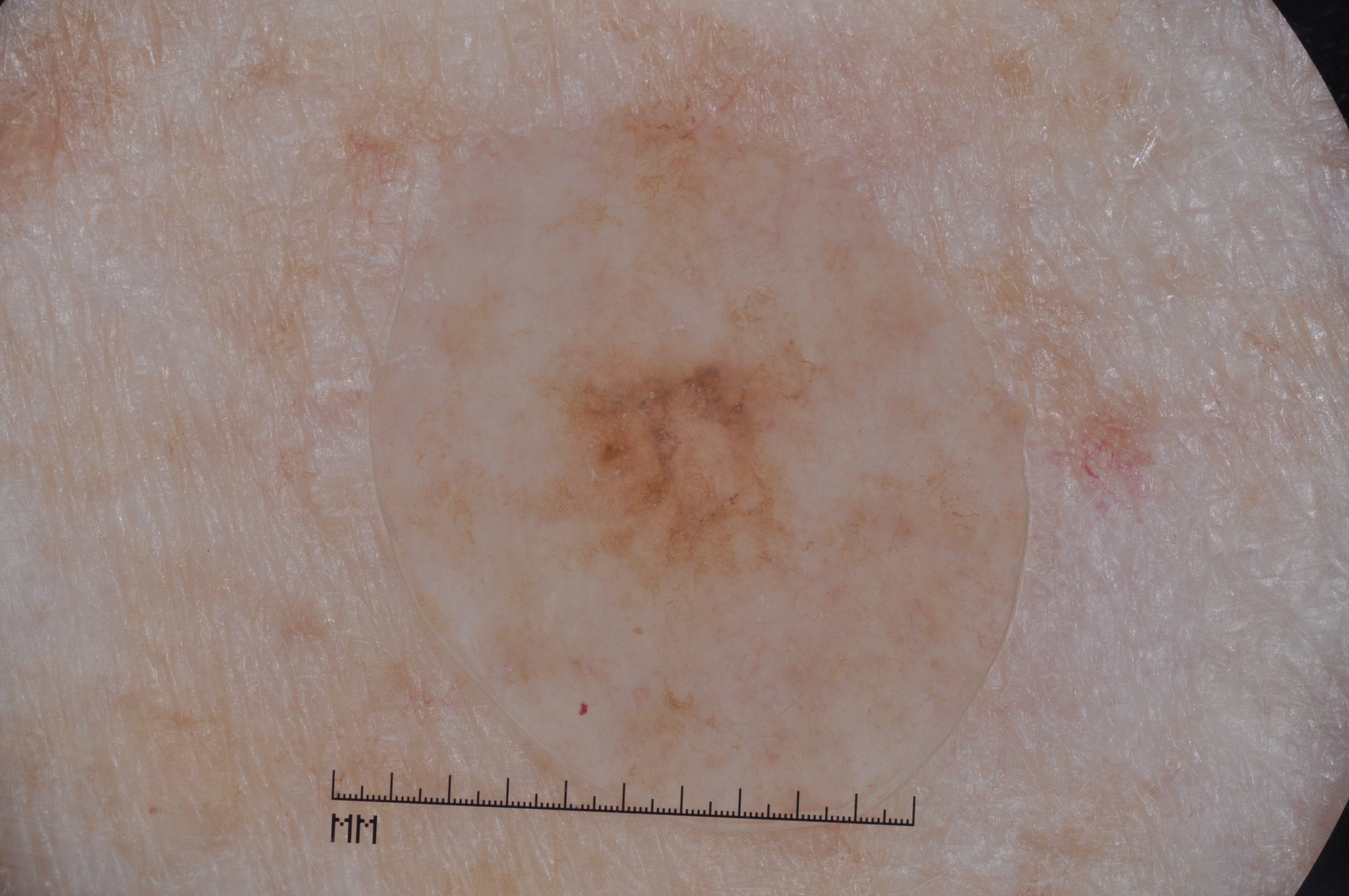{
  "image": {
    "modality": "dermoscopy"
  },
  "dermoscopic_features": {
    "present": [
      "milia-like cysts",
      "pigment network"
    ],
    "absent": [
      "streaks",
      "negative network"
    ]
  },
  "lesion_location": {
    "bbox_xyxy": [
      494,
      299,
      862,
      653
    ]
  },
  "lesion_extent": "moderate",
  "diagnosis": {
    "name": "melanoma",
    "malignancy": "malignant",
    "lineage": "melanocytic",
    "provenance": "histopathology"
  }
}